This image was taken at a distance, self-categorized by the patient as a rash, reported lesion symptoms include itching, the subject is female, the lesion involves the leg: 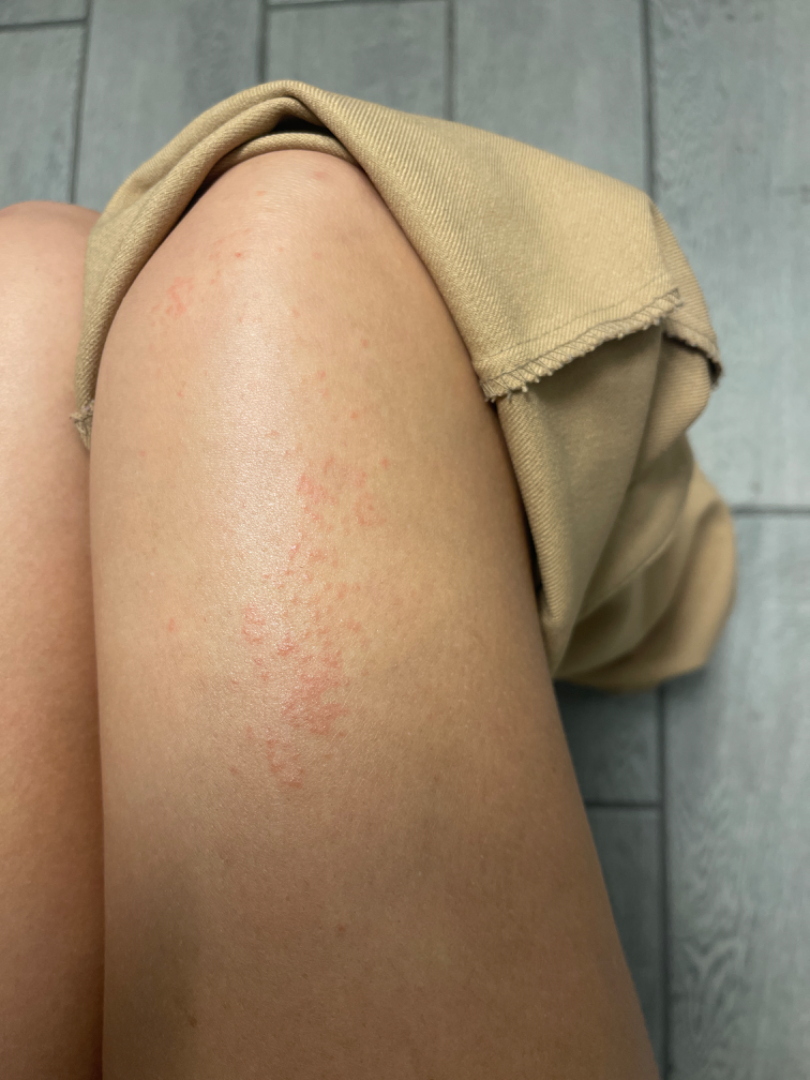Assessment: On remote dermatologist review: Eczema (50%); Allergic Contact Dermatitis (50%).